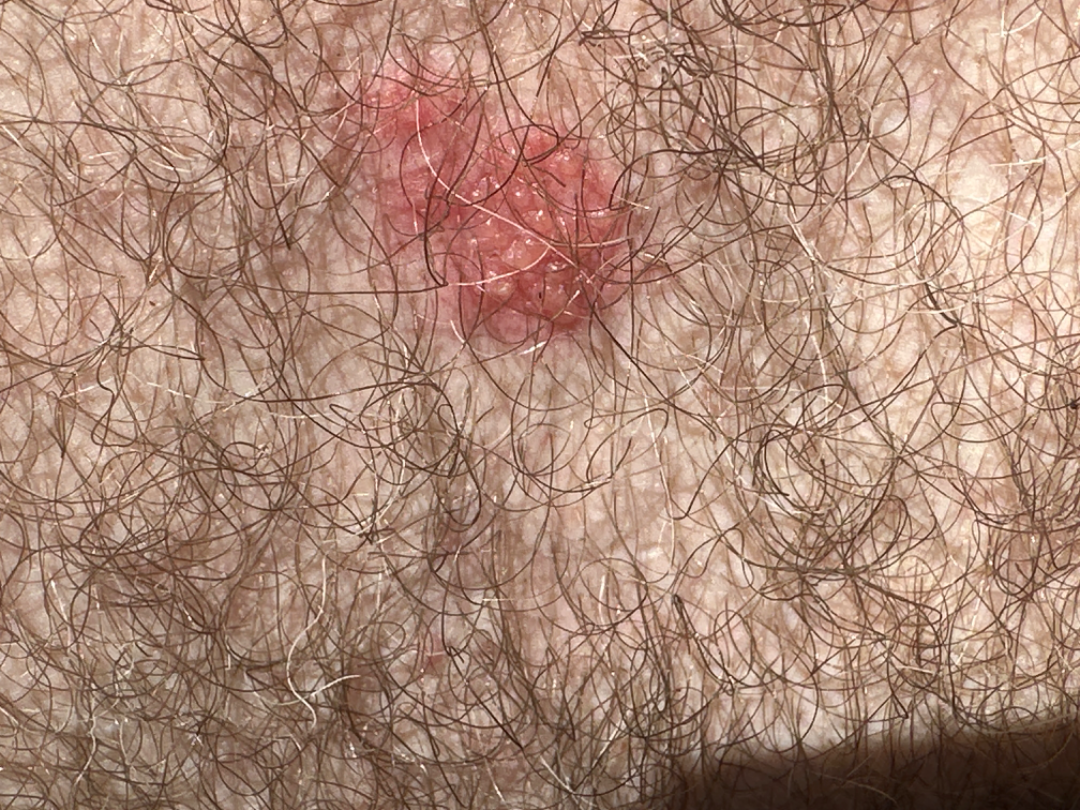Findings:
- lesion symptoms — itching, bothersome appearance and pain
- location — front of the torso and back of the torso
- history — about one day
- image framing — close-up
- self-categorized as — a rash
- texture — fluid-filled and raised or bumpy
- constitutional symptoms — chills, fatigue and fever
- differential — the primary impression is Condyloma acuminatum